Symptoms reported: enlargement and itching, an image taken at a distance, the contributor notes the lesion is raised or bumpy, the condition has been present for less than one week.
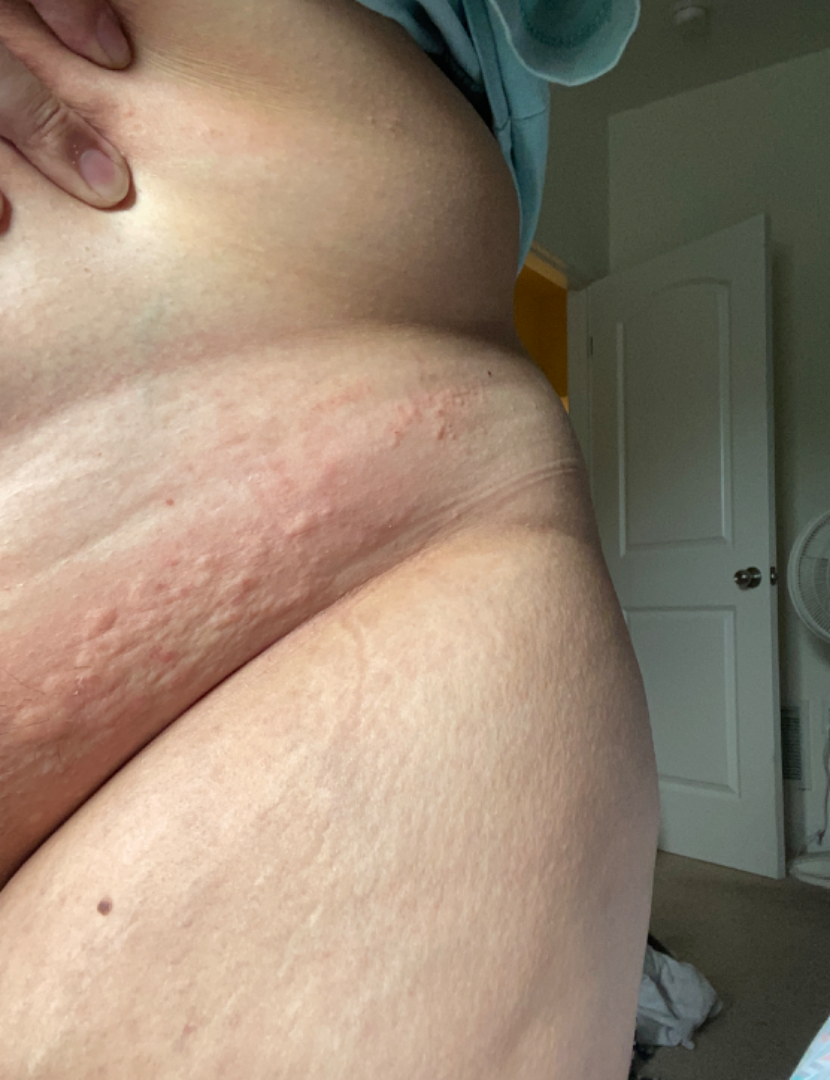The skin condition could not be confidently assessed from this image.